A male patient in their late 60s — 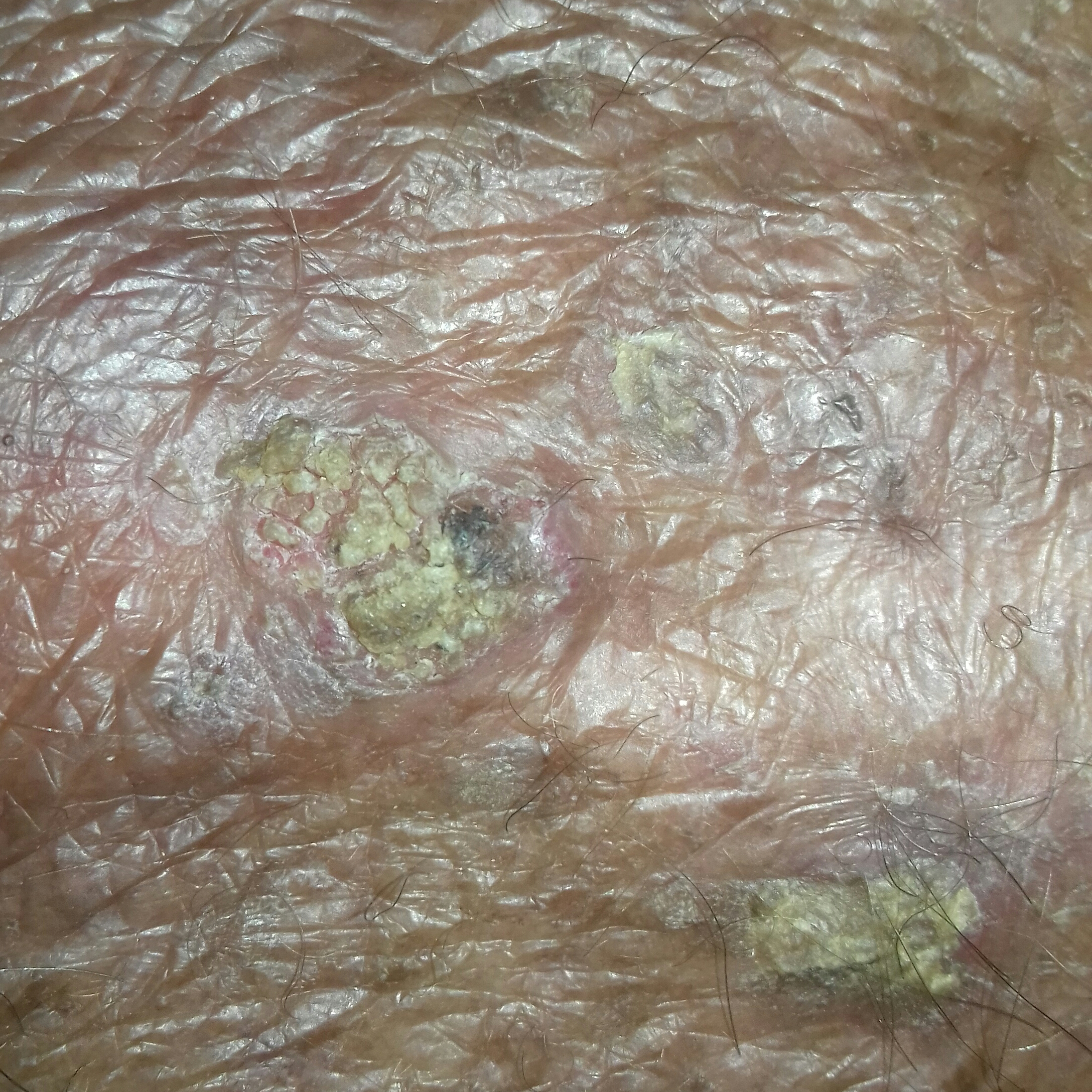Findings:
• impression: actinic keratosis (clinical consensus)